A close-up photograph:
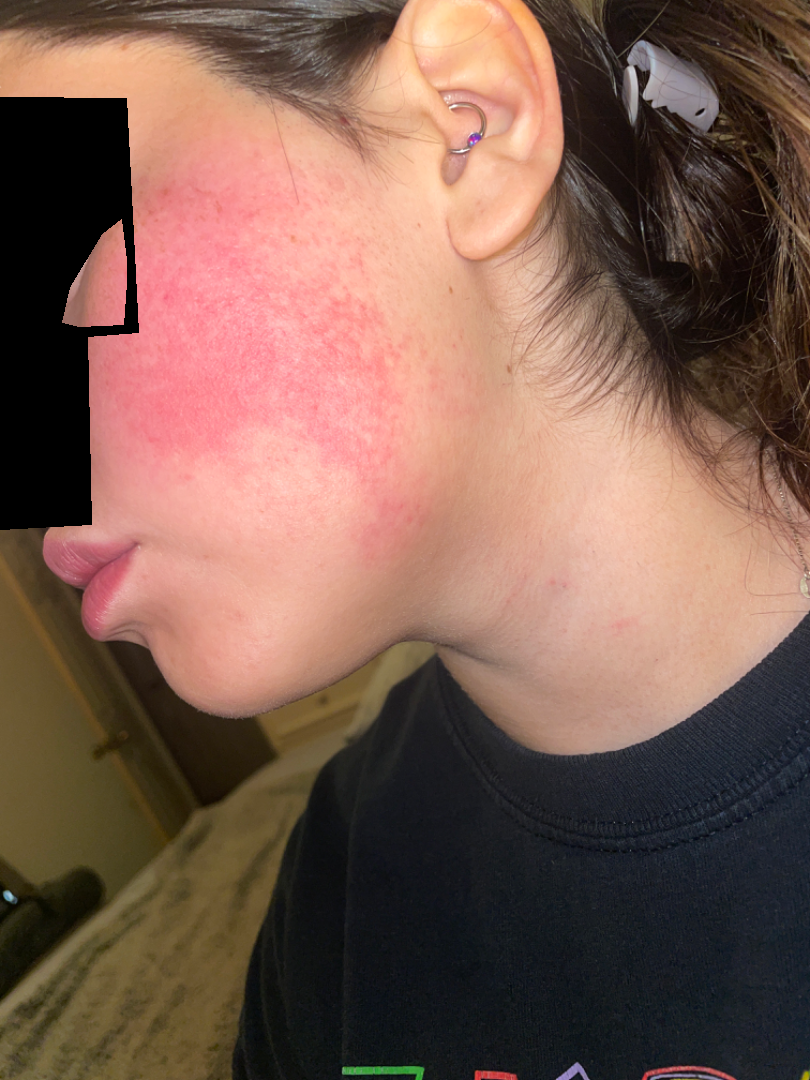assessment = not assessable; symptoms = bothersome appearance, burning and enlargement; lesion texture = flat; systemic symptoms = chills; self-categorized as = a rash; duration = about one day.